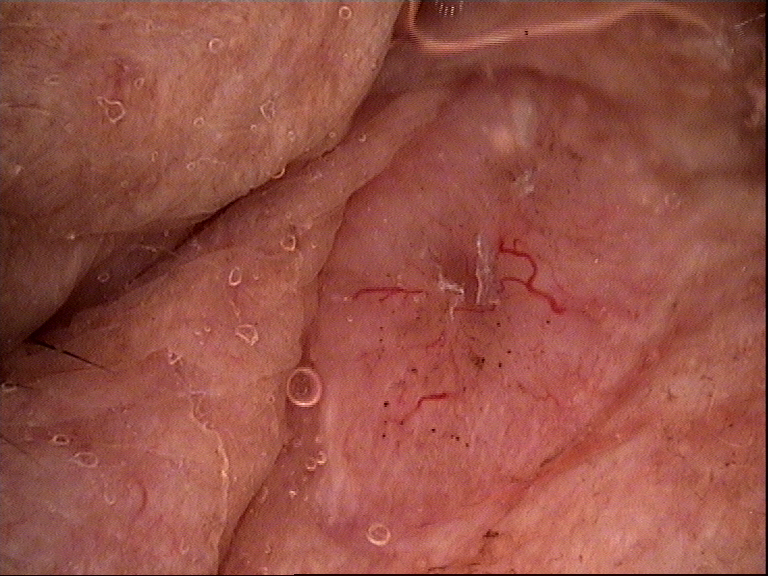{
  "image": "dermatoscopy",
  "lesion_type": {
    "main_class": "keratinocytic"
  },
  "diagnosis": {
    "name": "basal cell carcinoma",
    "code": "bcc",
    "malignancy": "malignant",
    "super_class": "non-melanocytic",
    "confirmation": "histopathology"
  }
}